This image was taken at a distance.
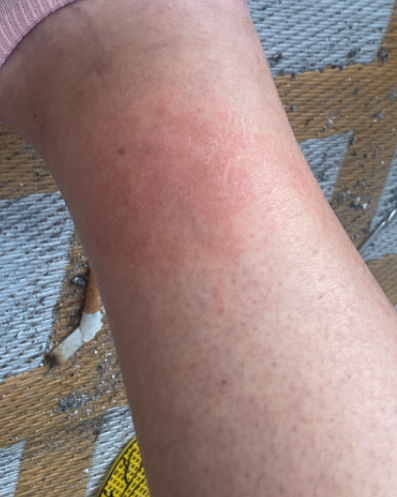Review:
On remote dermatologist review: the impression on review was Eczema.